Recorded as Fitzpatrick phototype II; by history, alcohol use, tobacco use, and prior skin cancer (patient or family); a male patient 73 years old; a clinical photograph showing a skin lesion: 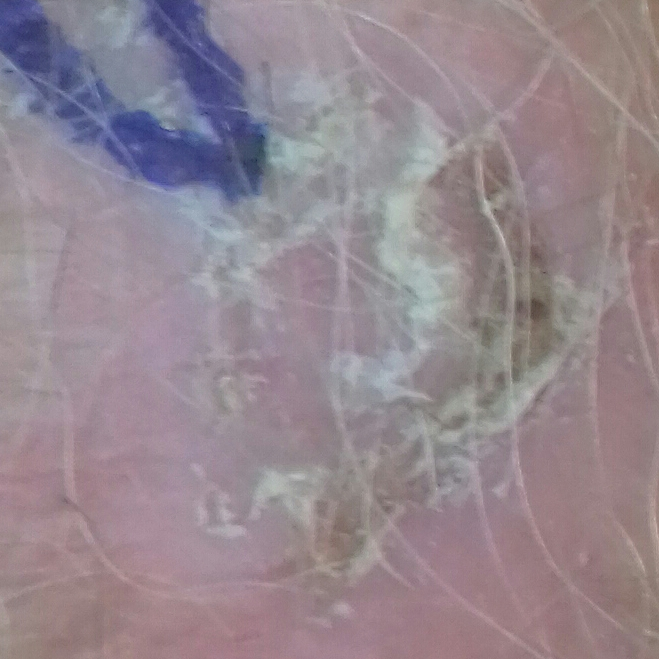The lesion was found on a hand.
Measuring about 25 × 18 mm.
By the patient's account, the lesion itches, but is not elevated and does not hurt.
Histopathological examination showed a malignancy — a basal cell carcinoma.